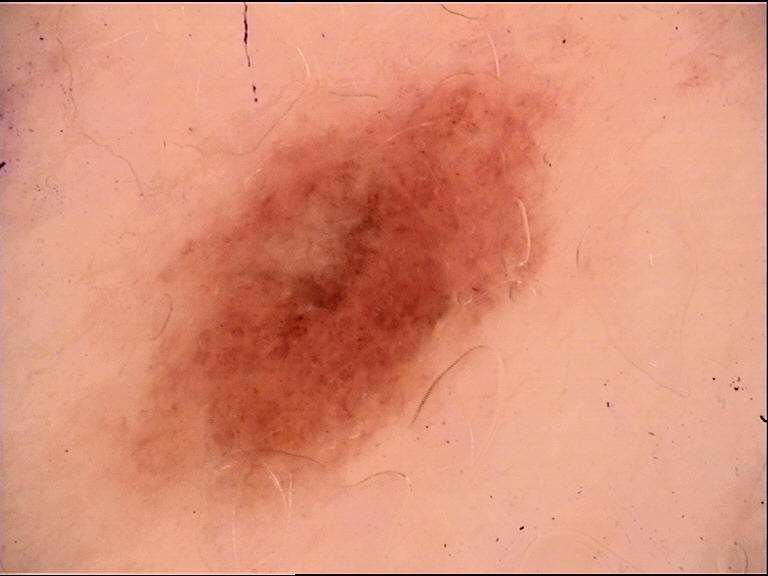Conclusion: The diagnosis was a dysplastic junctional nevus.